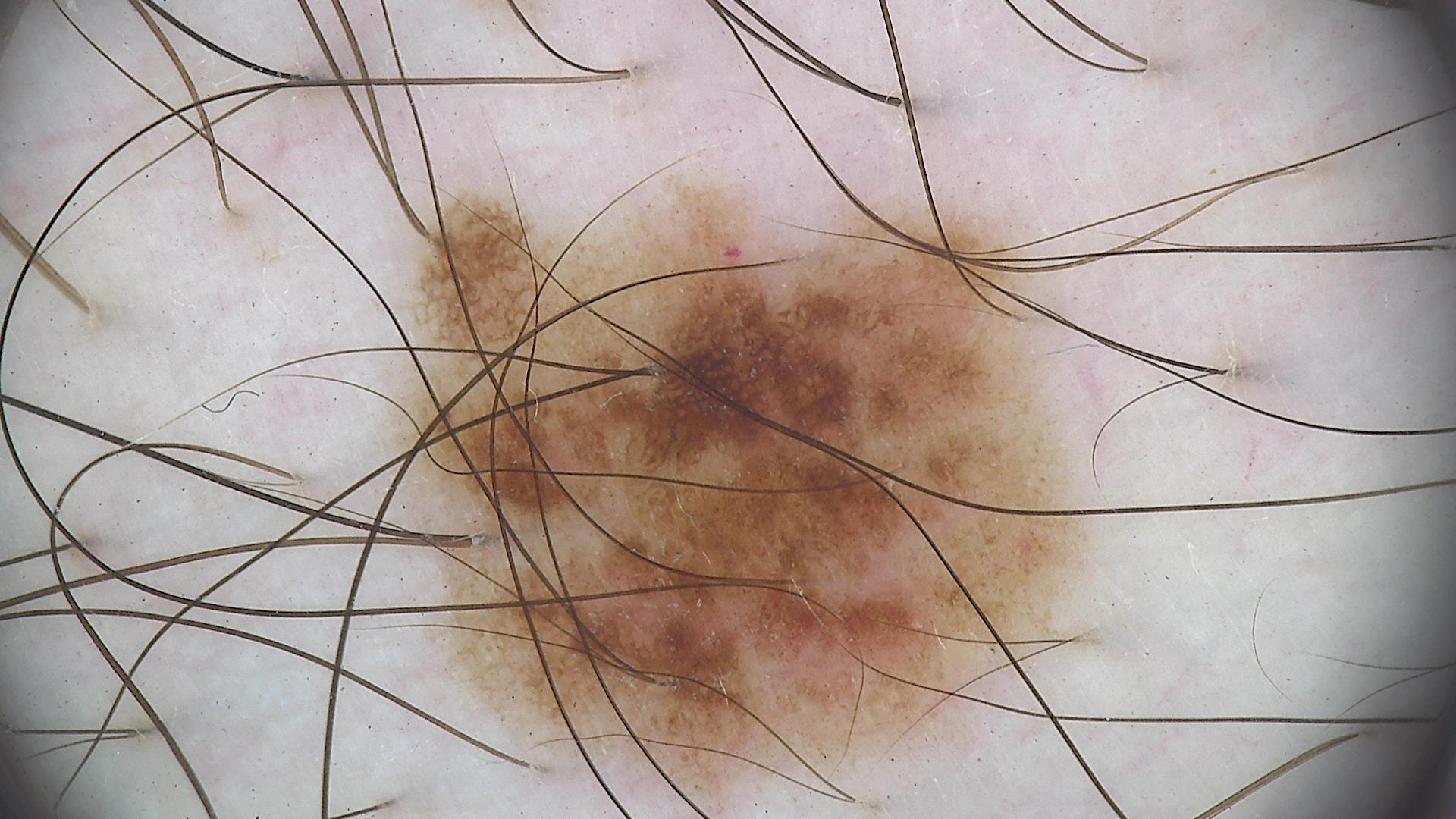image: dermoscopy
assessment: dysplastic junctional nevus (expert consensus)